The subject is a male roughly 60 years of age. A dermatoscopic image of a skin lesion.
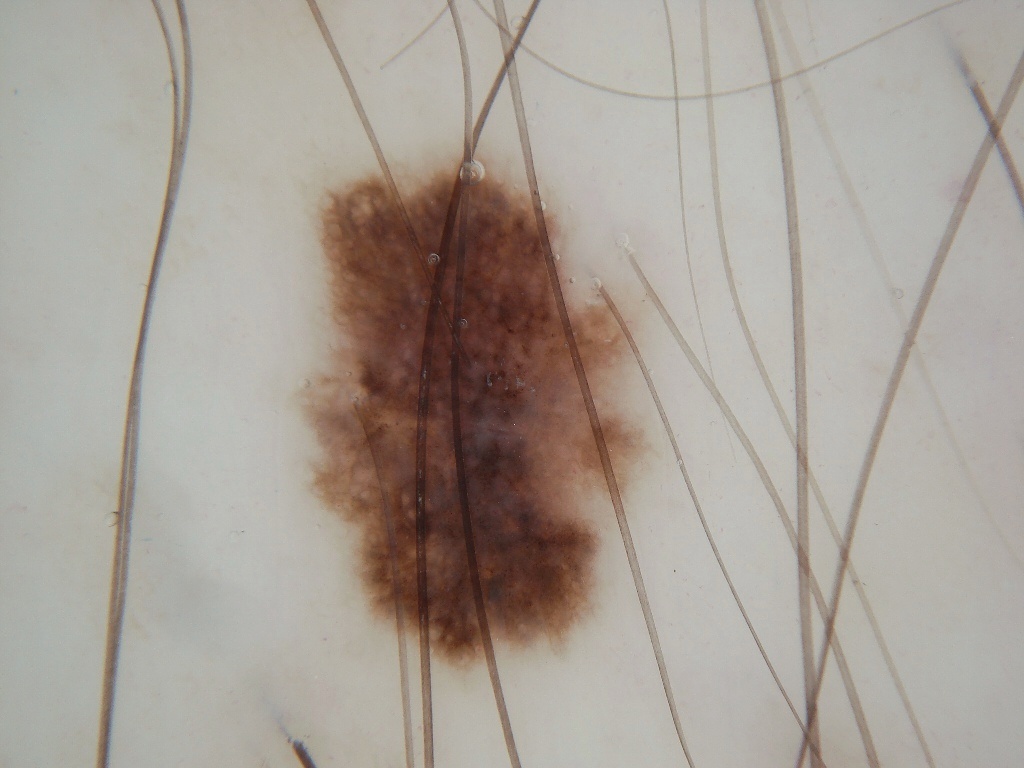<case>
<lesion_location>
  <bbox_xyxy>279, 141, 667, 686</bbox_xyxy>
</lesion_location>
<dermoscopic_features>
  <present>pigment network</present>
  <absent>milia-like cysts, streaks, globules, negative network</absent>
</dermoscopic_features>
<diagnosis>
  <name>melanocytic nevus</name>
  <malignancy>benign</malignancy>
  <lineage>melanocytic</lineage>
  <provenance>clinical</provenance>
</diagnosis>
</case>